A dermatoscopic image of a skin lesion; the patient was assessed as Fitzpatrick II; a female patient in their mid- to late 80s or older:
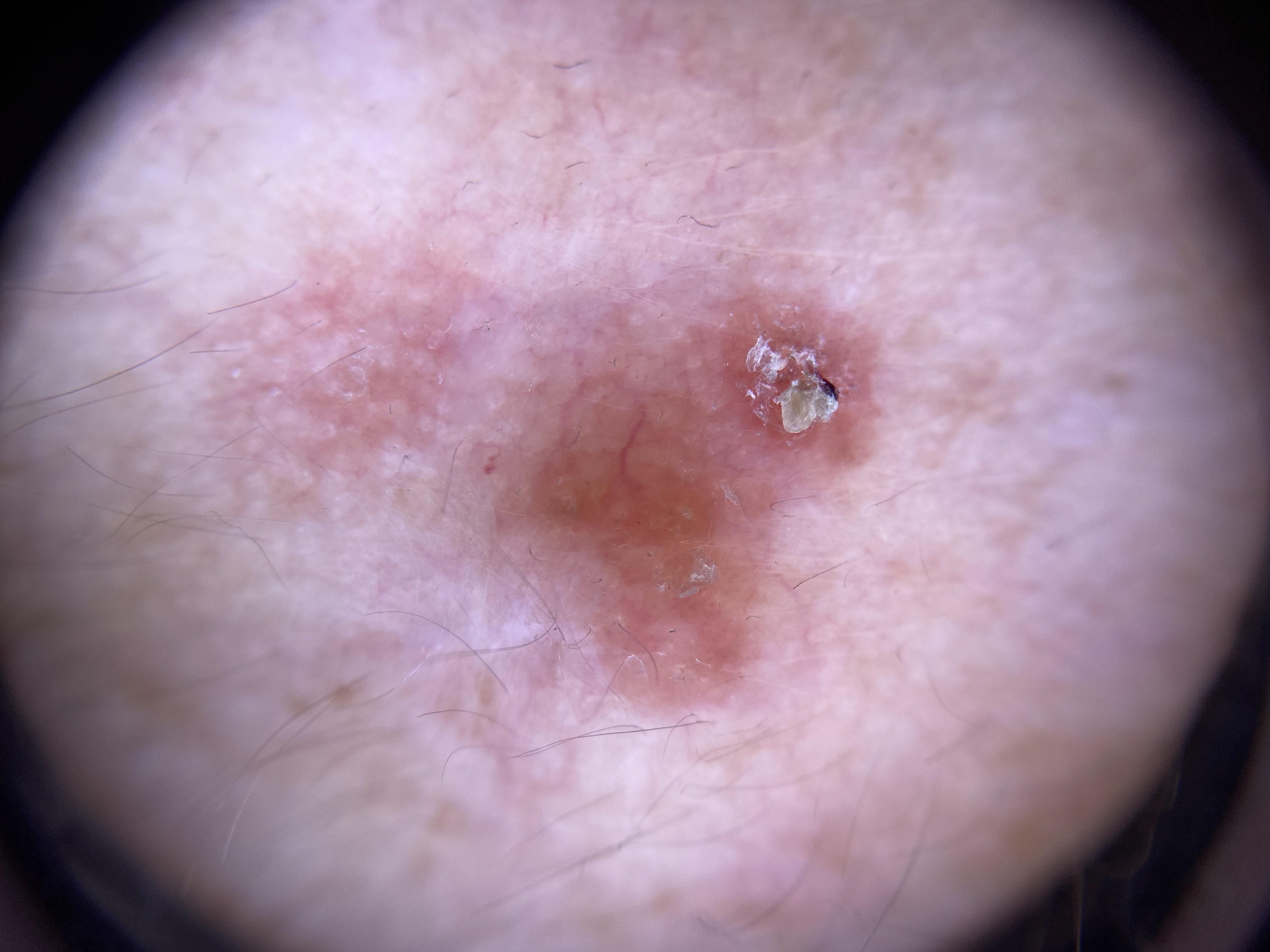Located on the head or neck. Histopathology confirmed a lesion of epidermal origin — a squamous cell carcinoma.